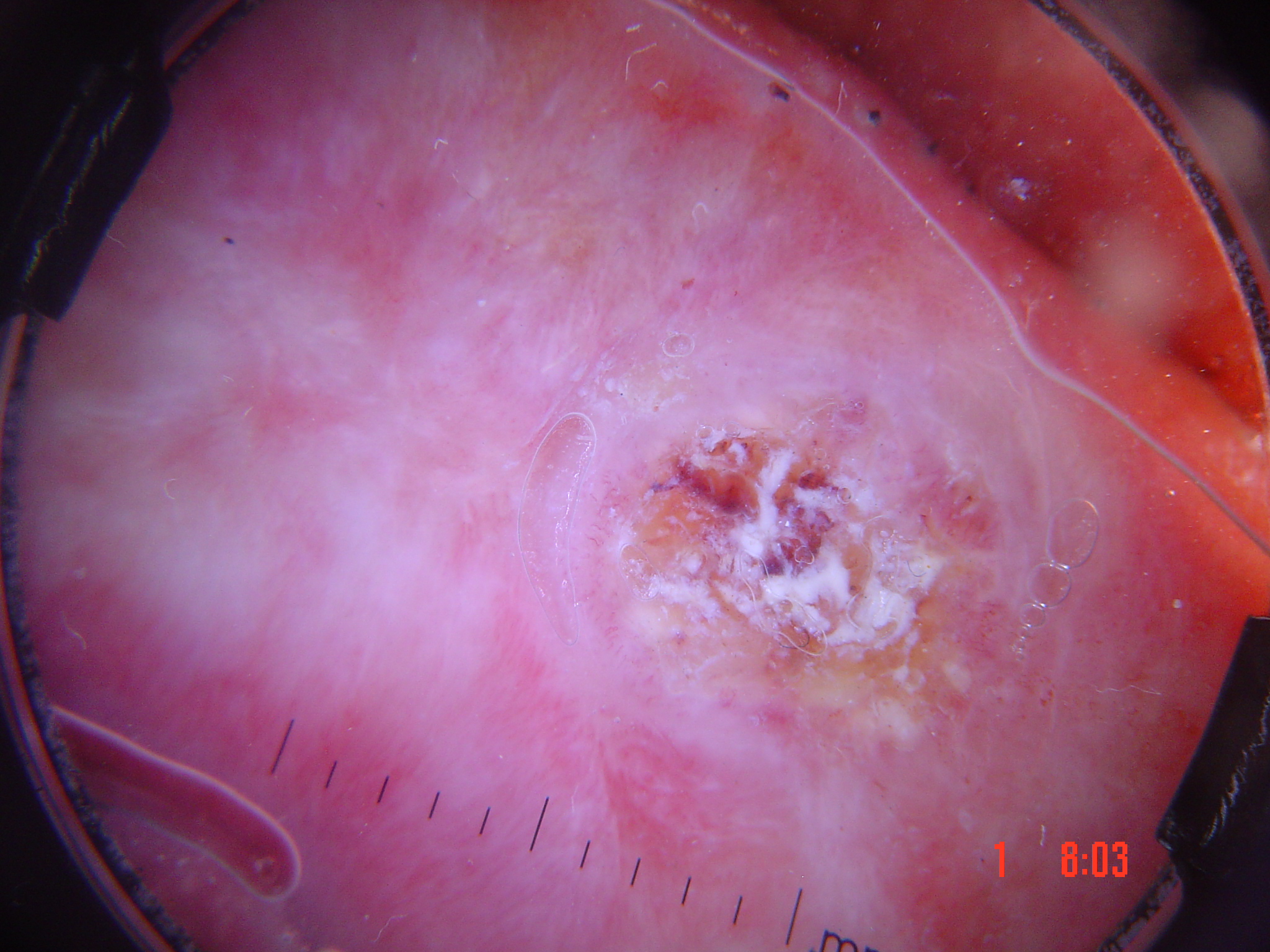image type = dermoscopy | class = squamous cell carcinoma (biopsy-proven).